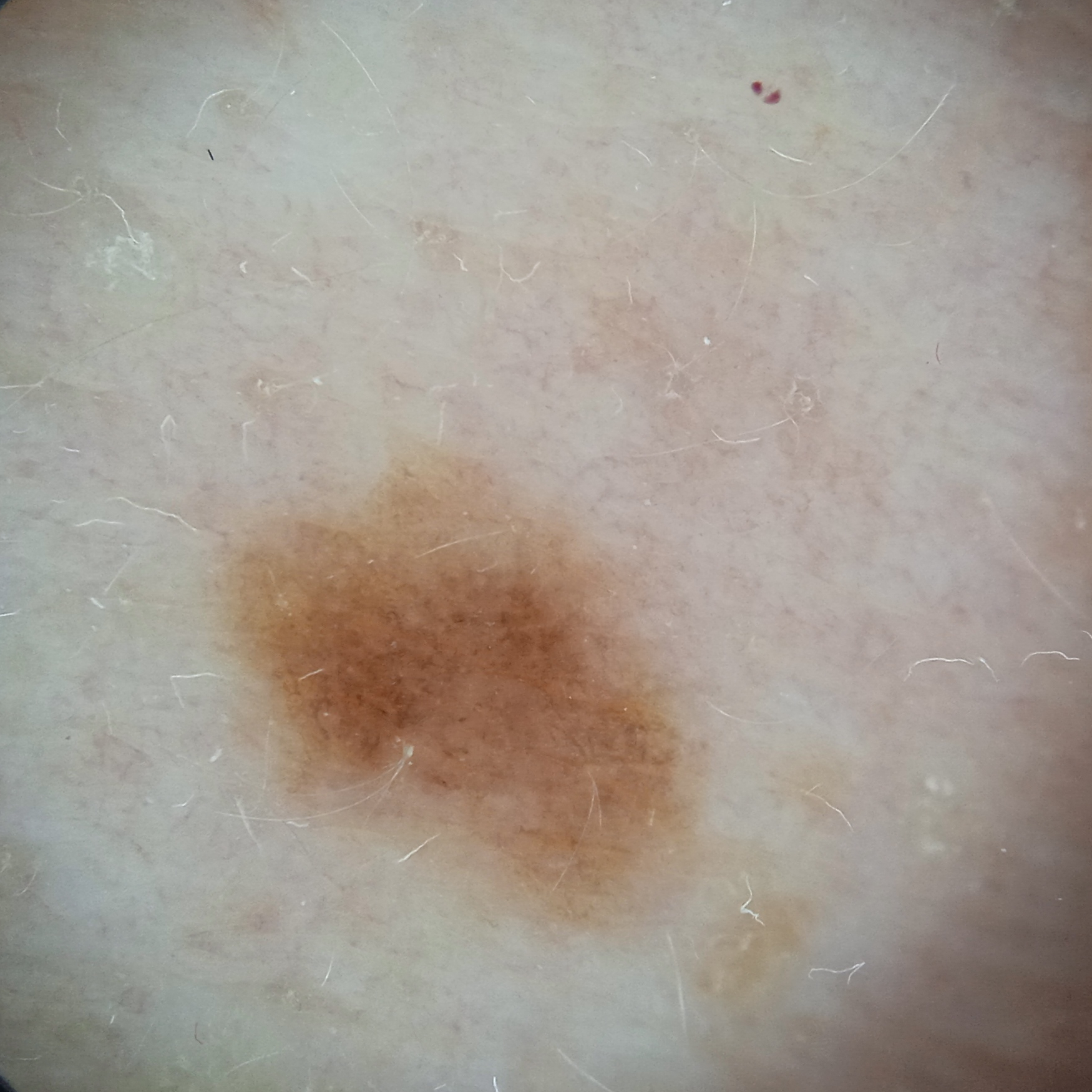- modality · dermatoscopic image
- nevus count · a moderate number of melanocytic nevi
- sun reaction · skin reddens painfully with sun exposure
- patient · female, 55 years of age
- relevant history · immunosuppression, a prior organ transplant
- referral context · research study (no referral diagnosis)
- location · the back
- size · 6.3 mm
- diagnostic label · melanocytic nevus (dermatologist consensus)